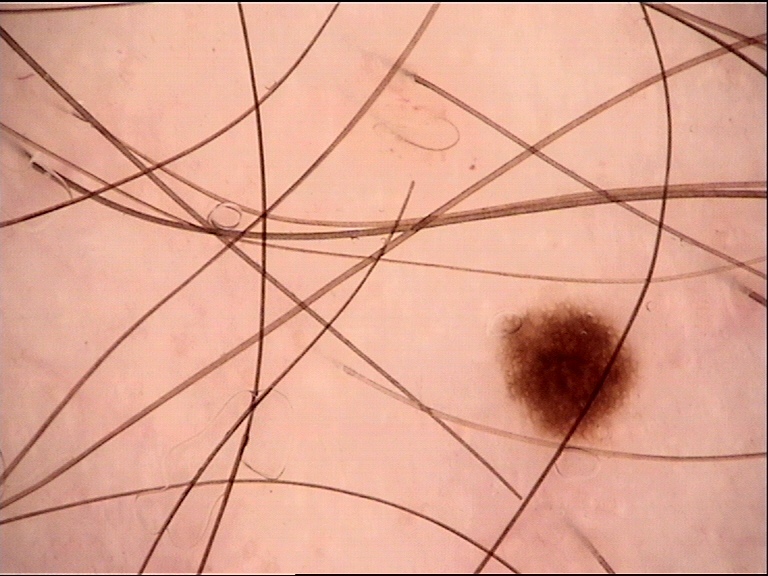Findings: A dermoscopic close-up of a skin lesion. Impression: Classified as a dysplastic junctional nevus.